The affected area is the arm; close-up view — 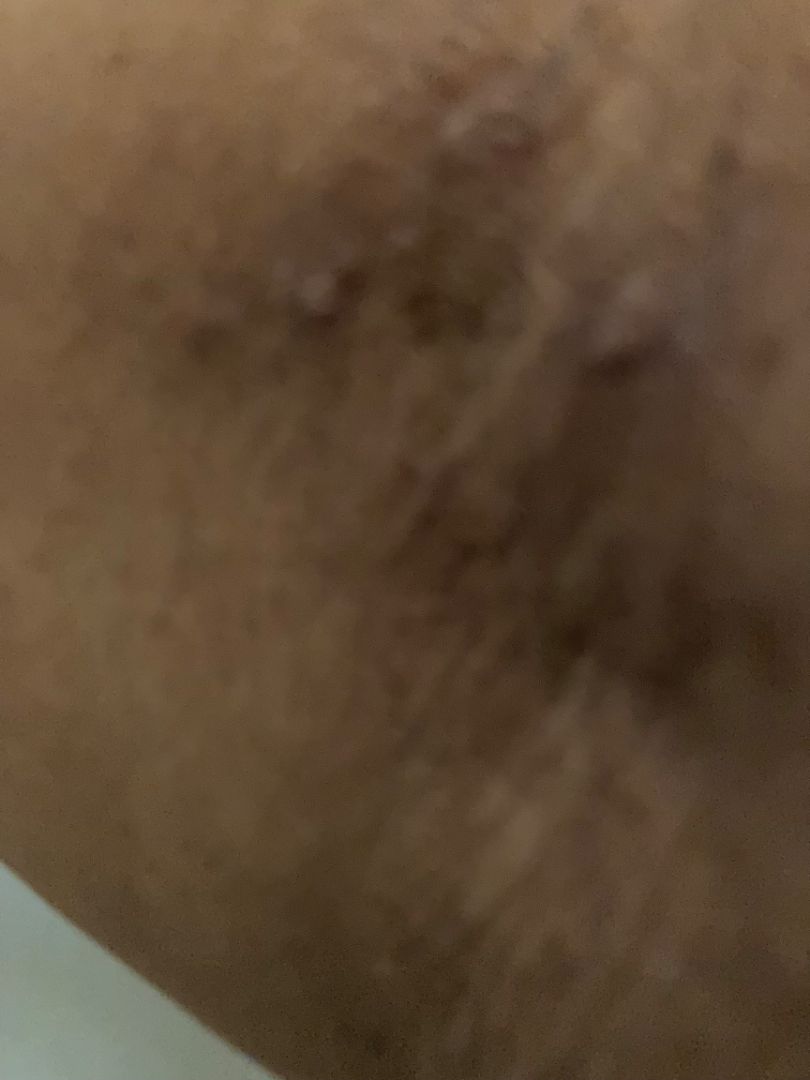assessment=not assessable
other reported symptoms=fatigue and joint pain
onset=one to three months
self-categorized as=a rash